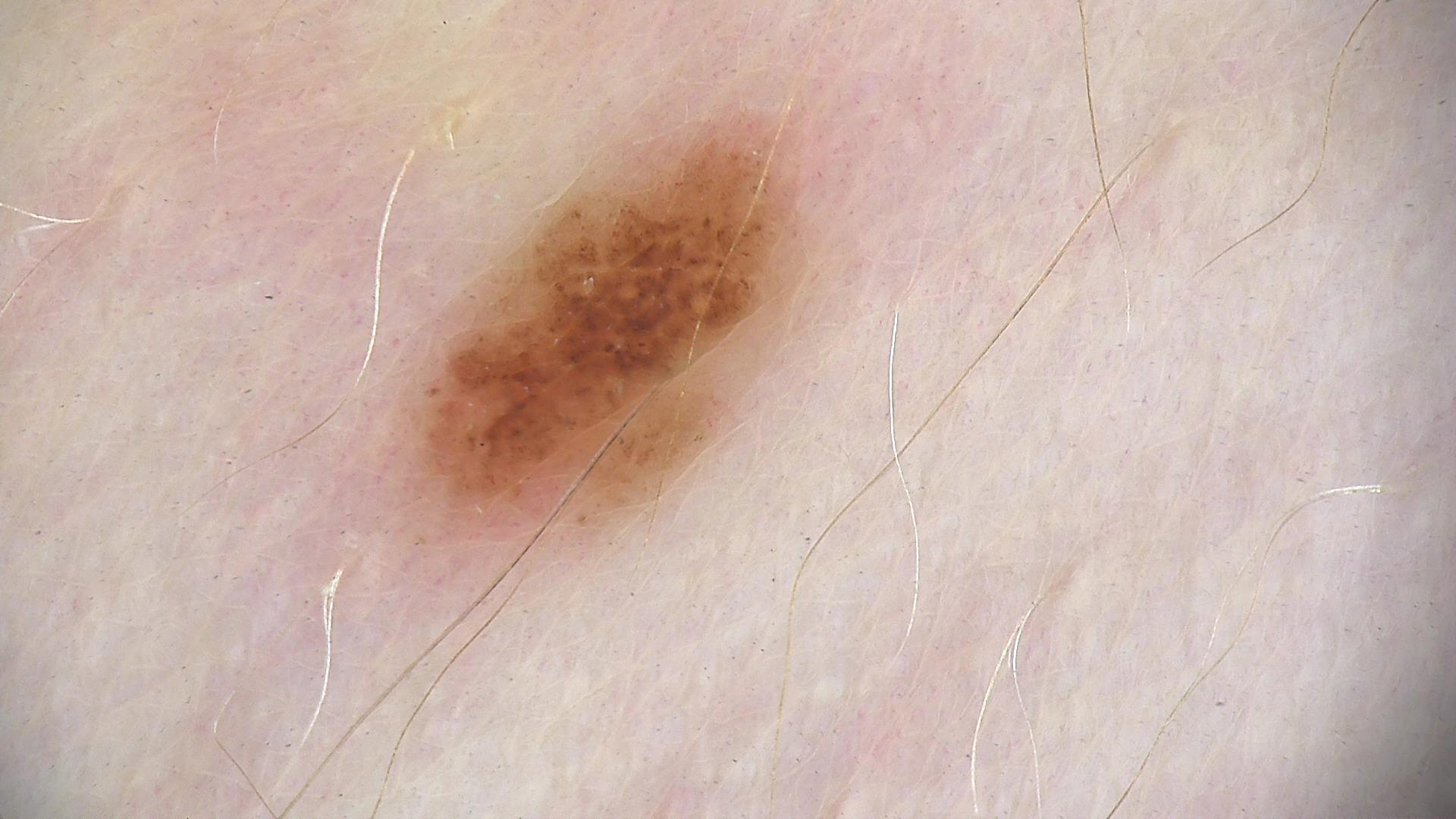A dermatoscopic image of a skin lesion. Classified as a benign lesion — a dysplastic junctional nevus.